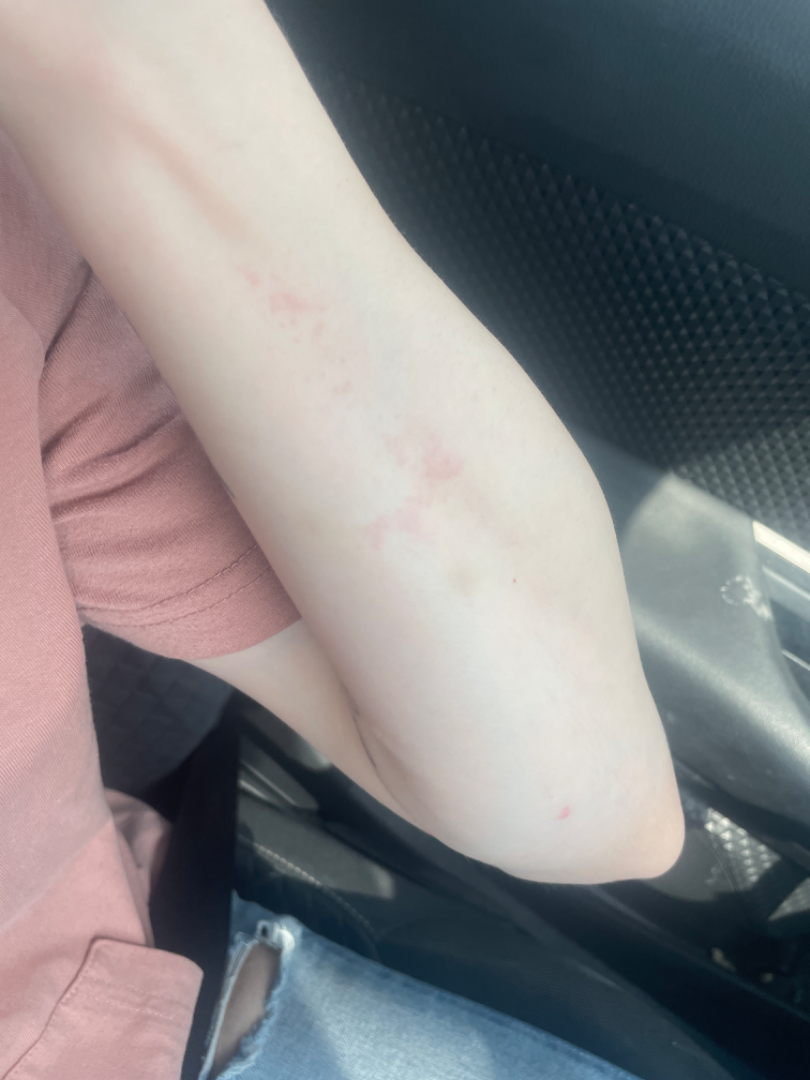{
  "assessment": "unable to determine",
  "shot_type": "at a distance",
  "body_site": "arm"
}